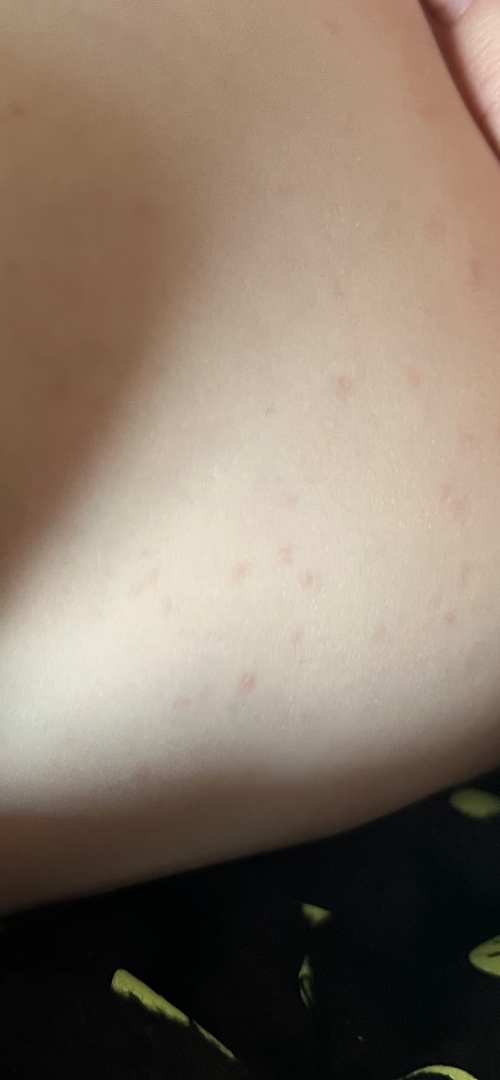Findings: The condition could not be reliably identified from the image. Background: The photograph was taken at an angle.